A close-up photograph; the affected area is the arm; the patient reports the lesion is raised or bumpy; the patient described the issue as a rash; present for less than one week:
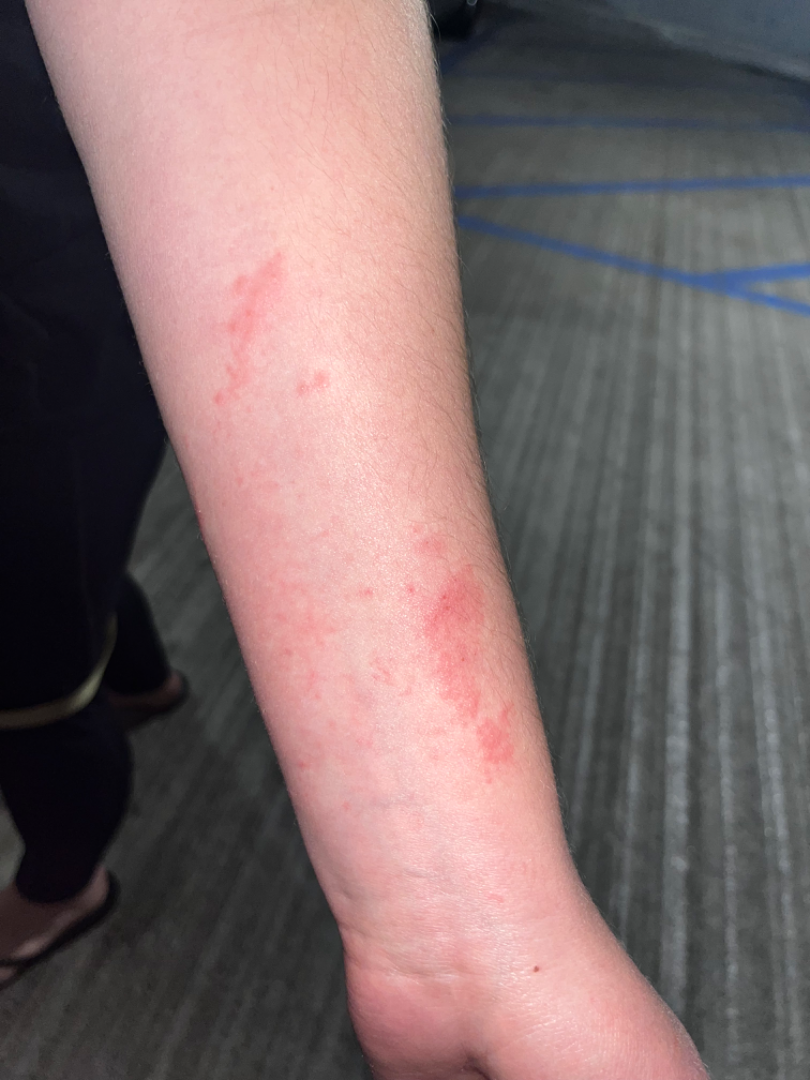Acute dermatitis, NOS (possible); Allergic Contact Dermatitis (possible).